A wide-field clinical photograph of a skin lesion; a male patient aged 68 to 72; the patient is skin type II — 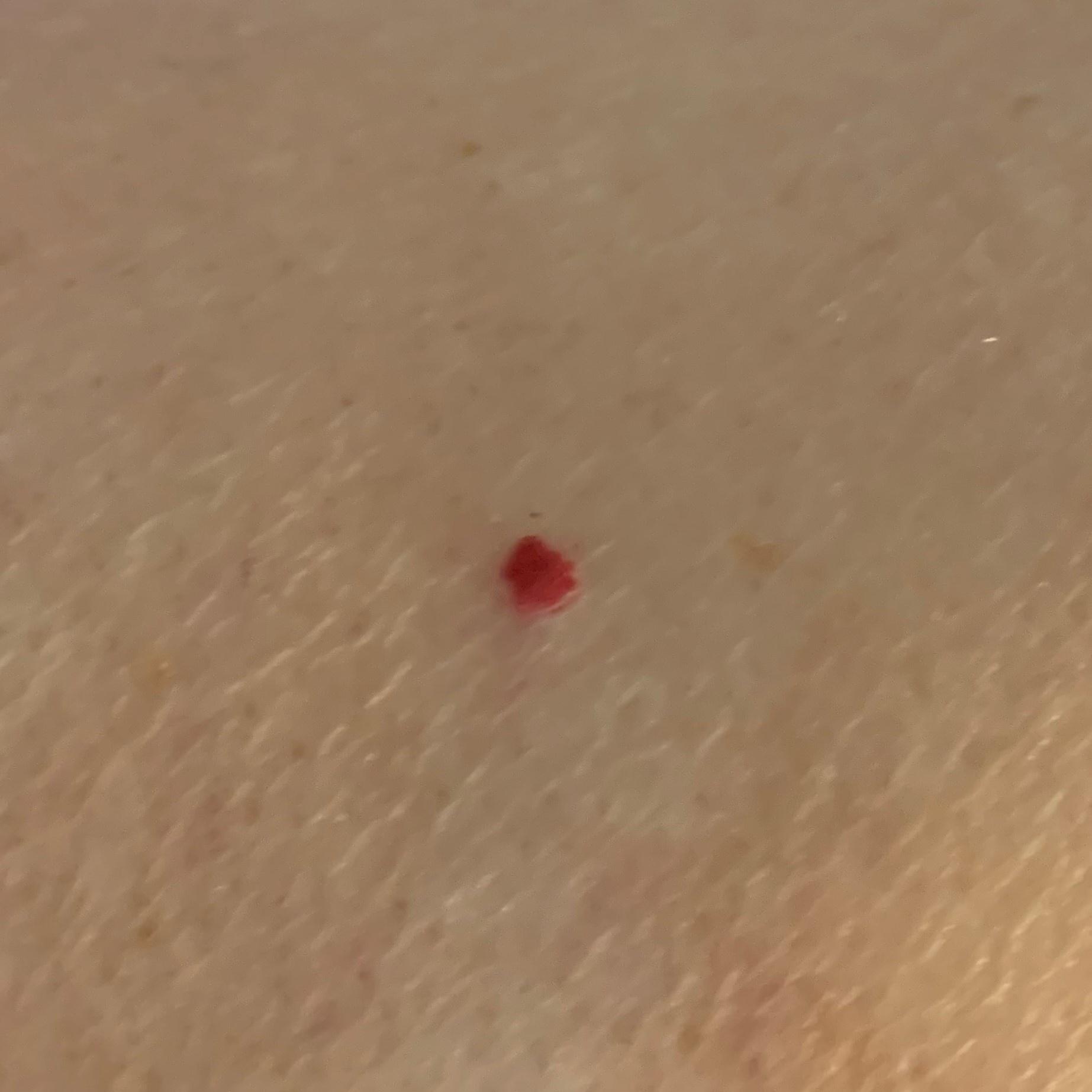The lesion is located on an upper extremity. The clinical impression was a benign vascular lesion.